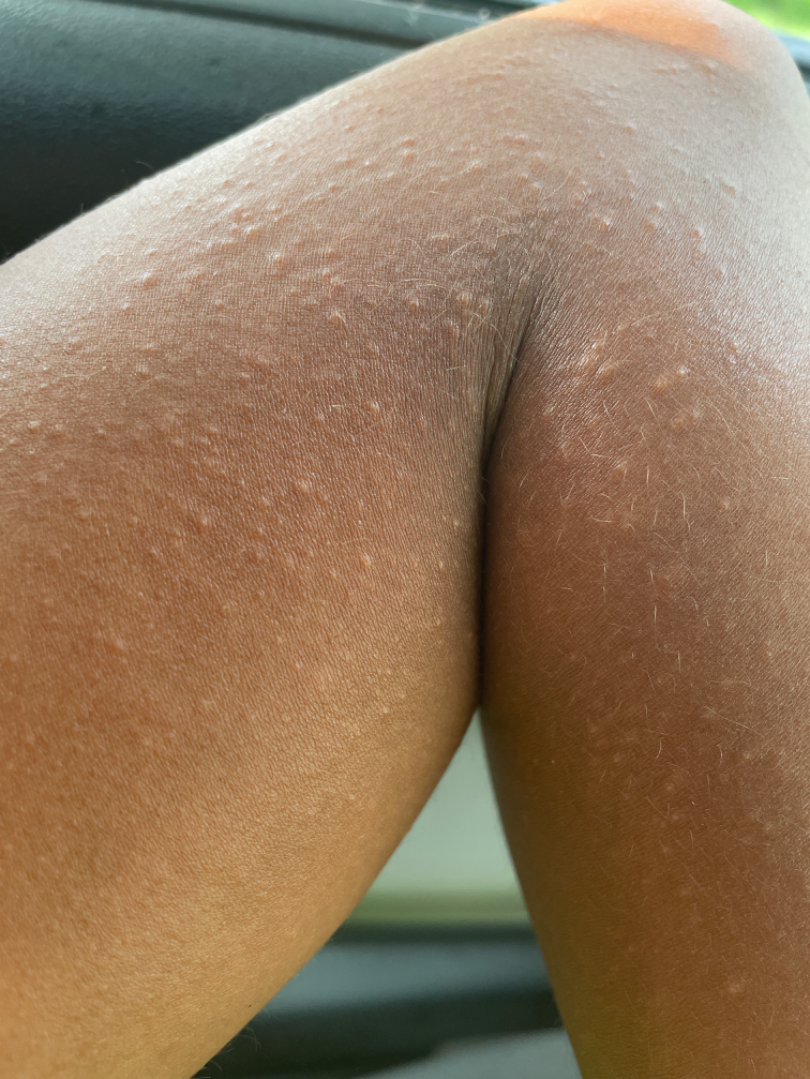  texture: raised or bumpy
  body_site:
    - head or neck
    - arm
  shot_type: close-up
  differential:
    leading:
      - Eczema
    considered:
      - Lichen nitidus
      - Allergic Contact Dermatitis